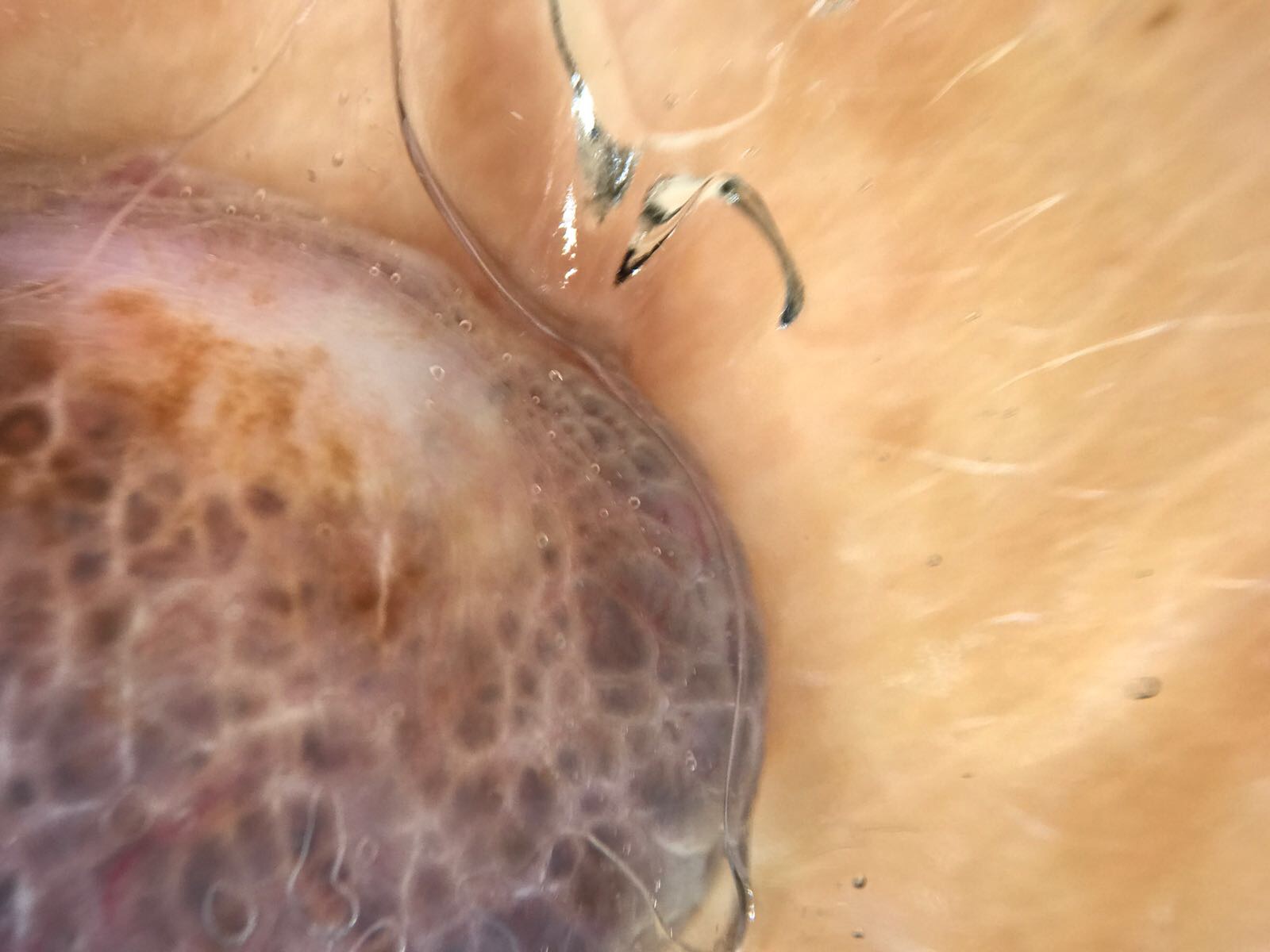diagnostic label — melanoma (biopsy-proven).